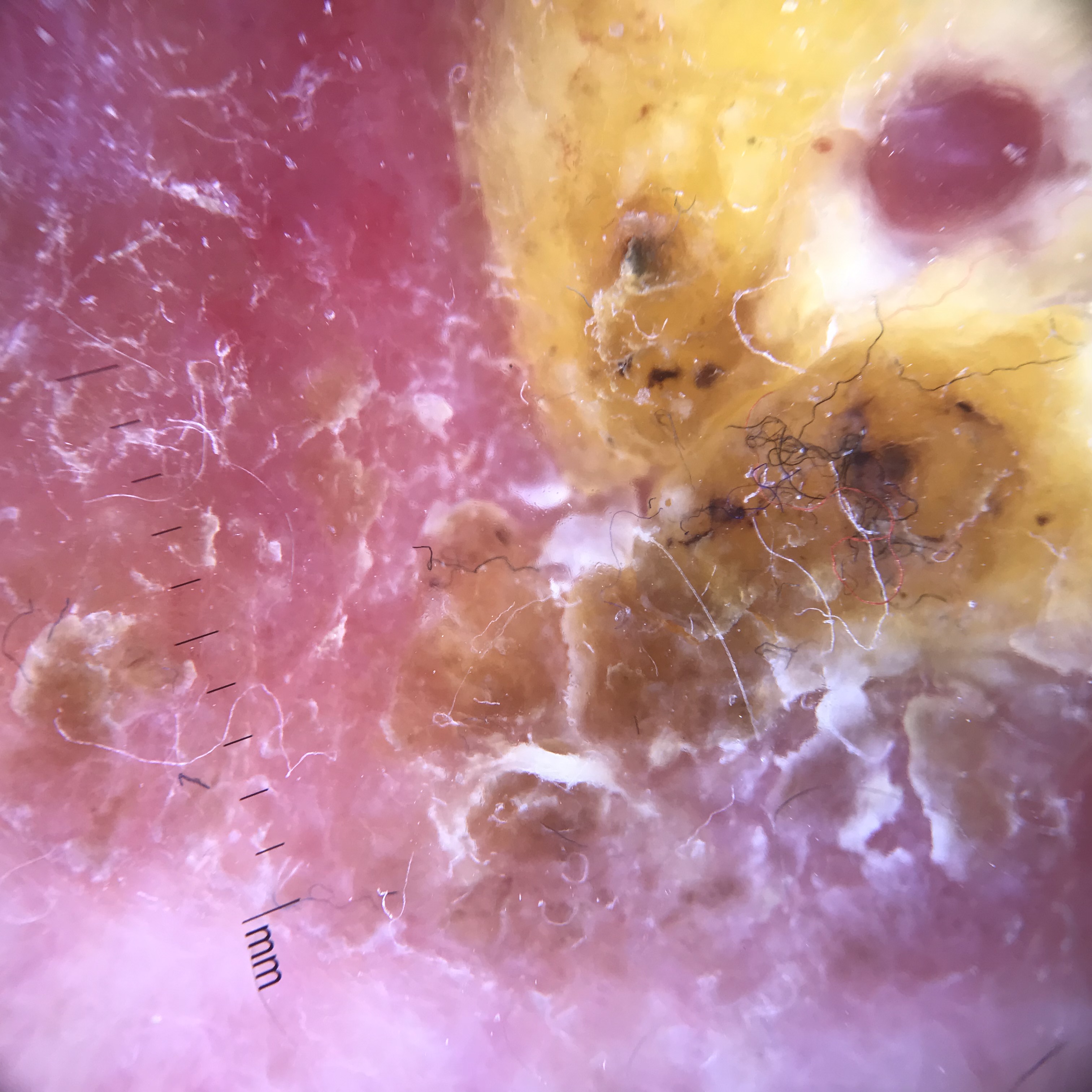A skin lesion imaged with a dermatoscope. Biopsy-confirmed as a keratinocytic lesion — a squamous cell carcinoma.